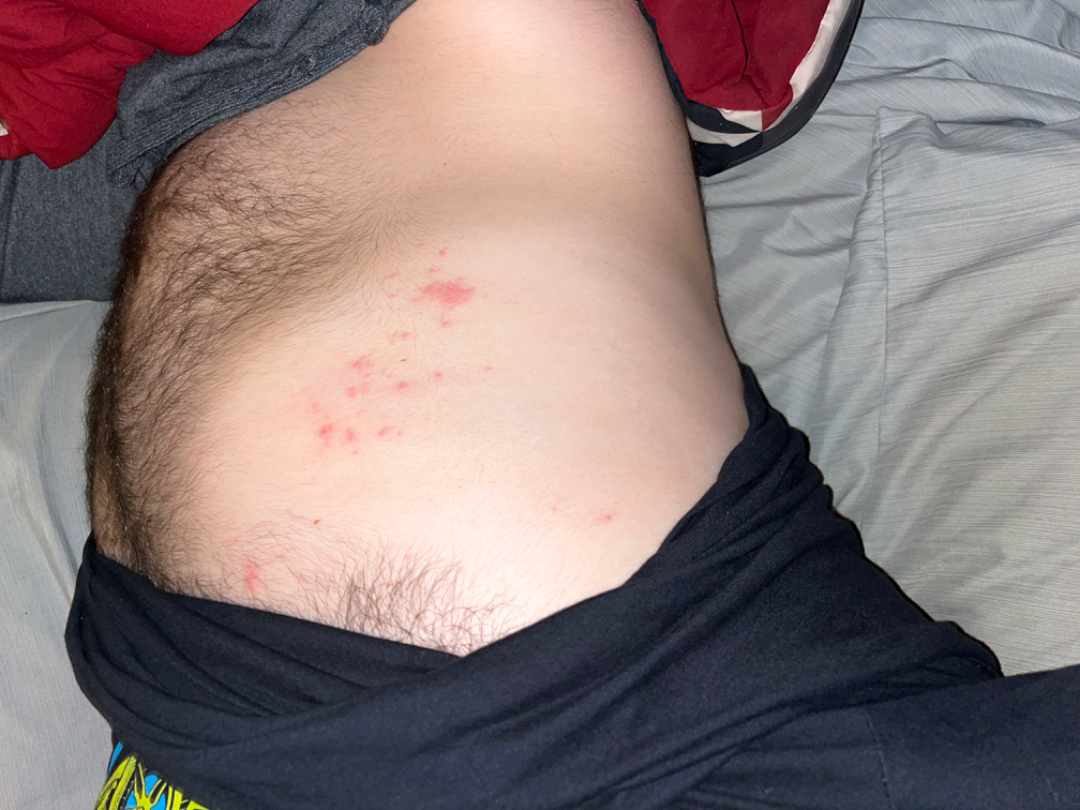The photo was captured at a distance. The lesion is described as raised or bumpy. Reported duration is one to four weeks. Self-categorized by the patient as a rash. Male contributor, age 18–29. The affected area is the head or neck, top or side of the foot, front of the torso, leg and arm. No constitutional symptoms were reported. On remote review of the image, the impression was split between Folliculitis, Herpes Zoster and Allergic Contact Dermatitis.